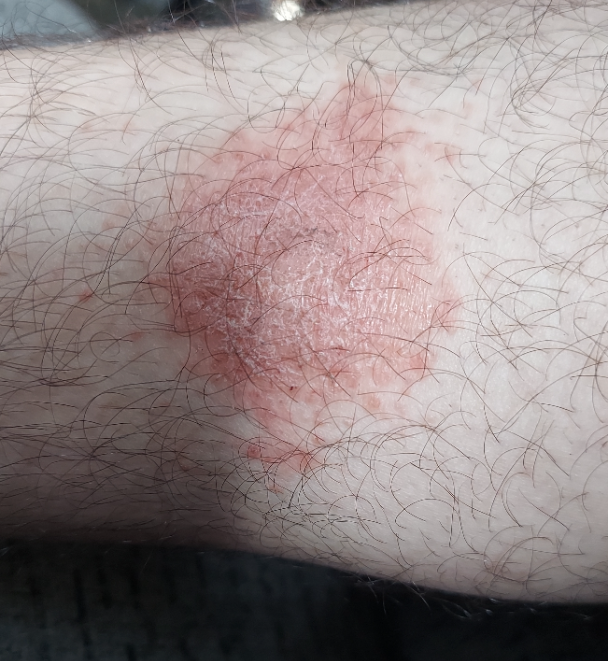The photograph is a close-up of the affected area.
The affected area is the leg.
The reviewing clinician's impression was: most consistent with Eczema.